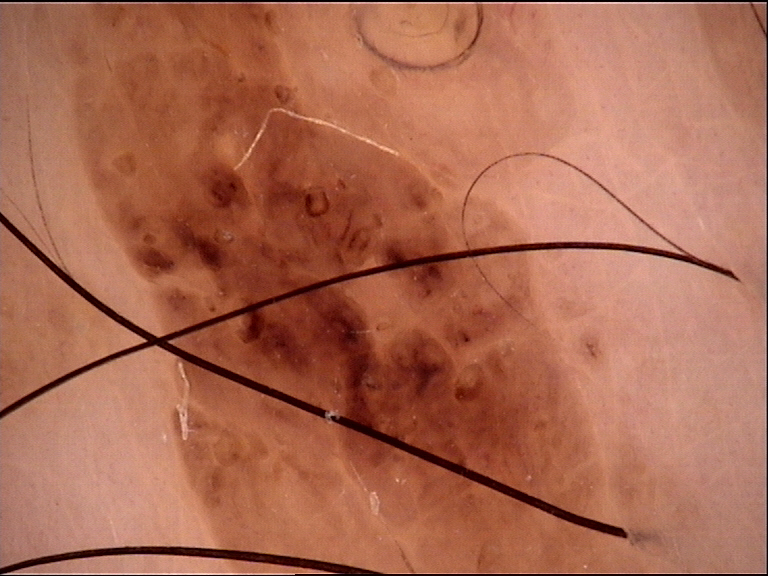Case:
– diagnosis — compound nevus (expert consensus)